A female patient aged around 85 or older; a skin lesion imaged with contact-polarized dermoscopy: 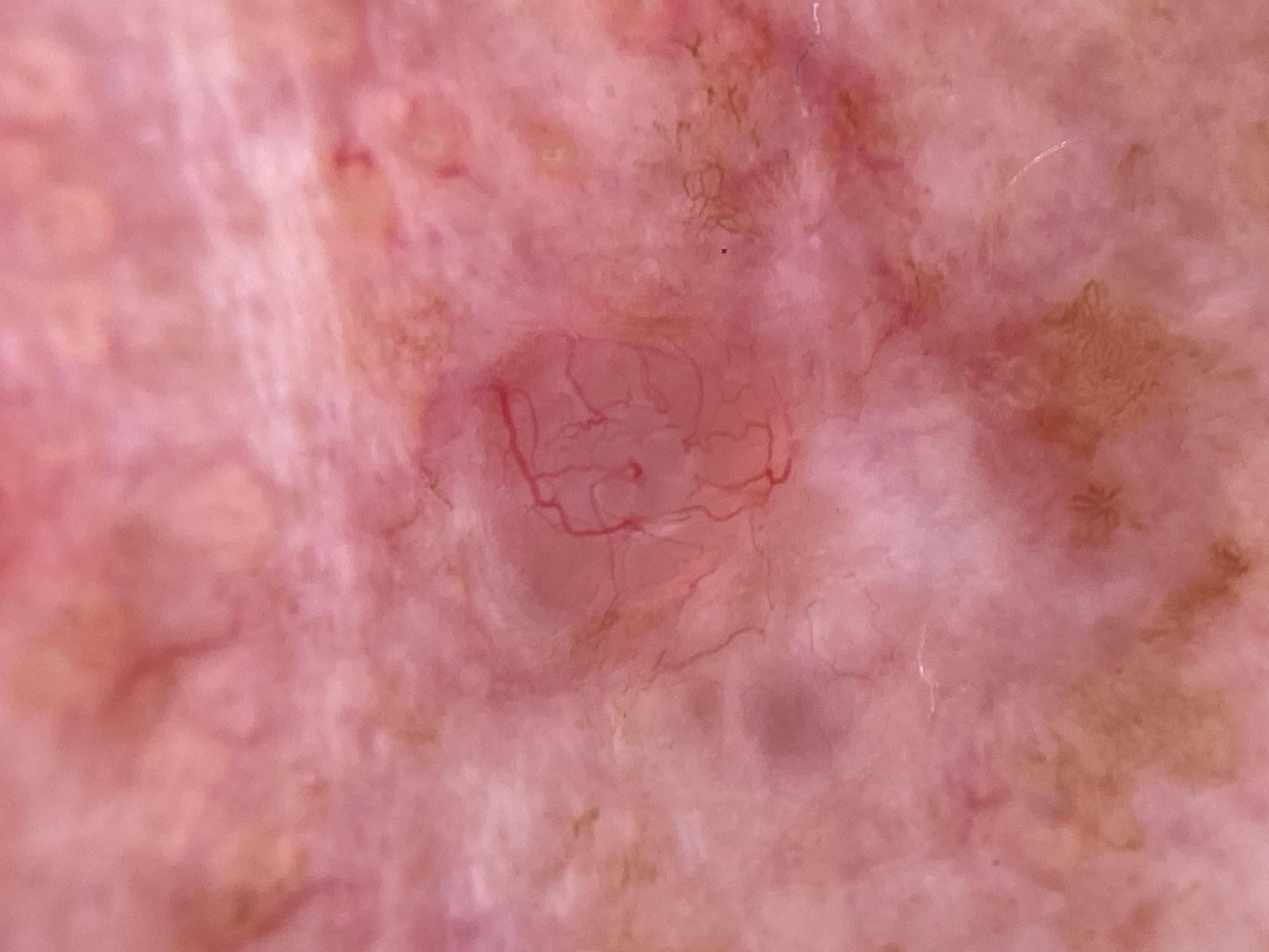Case summary:
The lesion was found on the head or neck.
Conclusion:
The biopsy diagnosis was a malignant, adnexal lesion — a basal cell carcinoma.